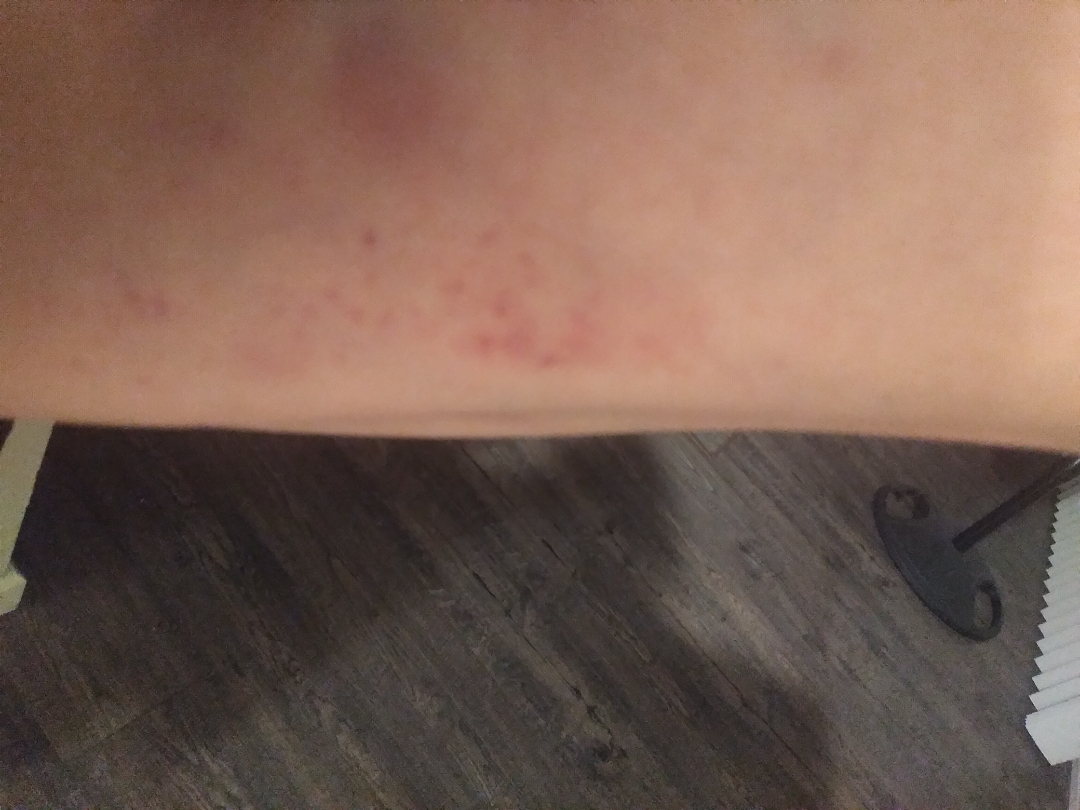The case was difficult to assess from the available photograph. Lay graders estimated a Monk skin tone scale of 2. The patient considered this a rash. No associated systemic symptoms reported. A close-up photograph. The patient reported no relevant symptoms from the lesion. The lesion involves the leg. The lesion is described as rough or flaky. Reported duration is about one day.